A macroscopic clinical photograph of a skin lesion; a male patient aged 54; a moderate number of moles by the patient's own estimate; imaged for a research study, with no referral diagnosis recorded; the patient says their skin tans without first burning: 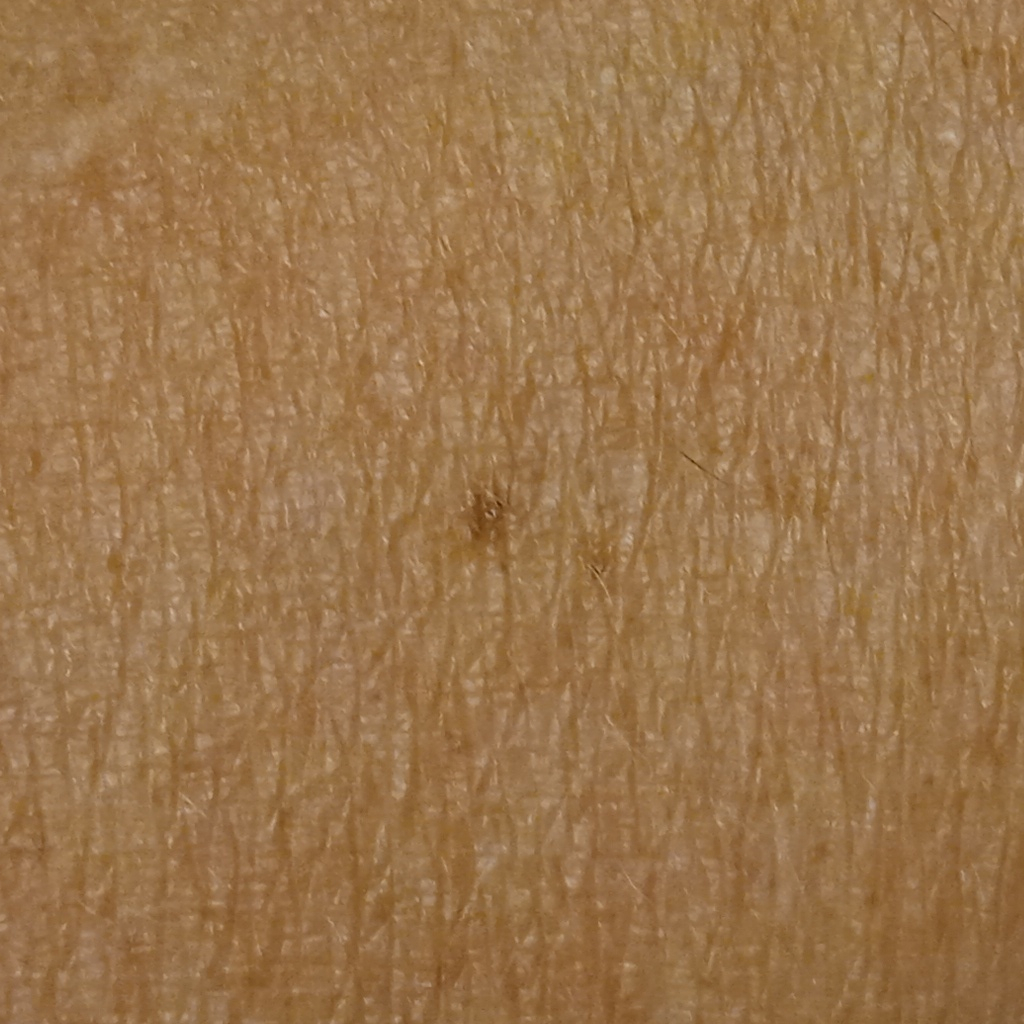Findings:
The lesion is on an arm. The lesion measures approximately 2.6 mm.
Impression:
The consensus diagnosis for this lesion was a melanocytic nevus.